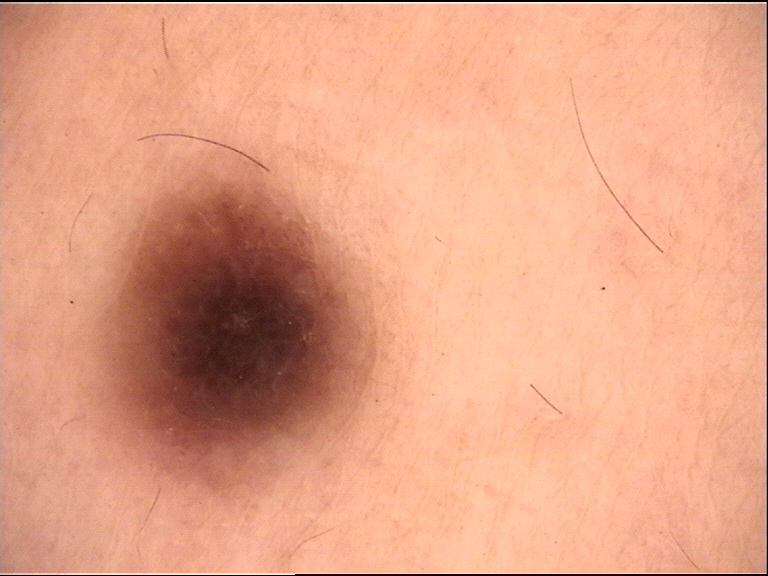Classified as a junctional nevus.